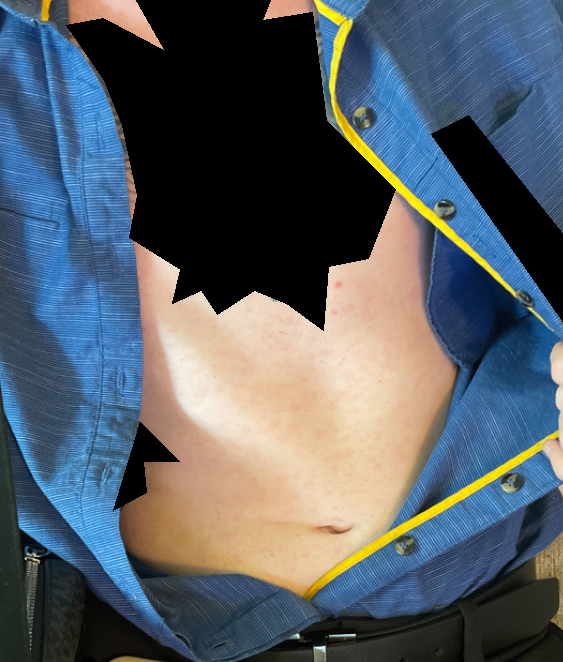view — at a distance | impression — Drug Rash and Viral Exanthem were each considered, in no particular order; lower on the differential is Folliculitis.